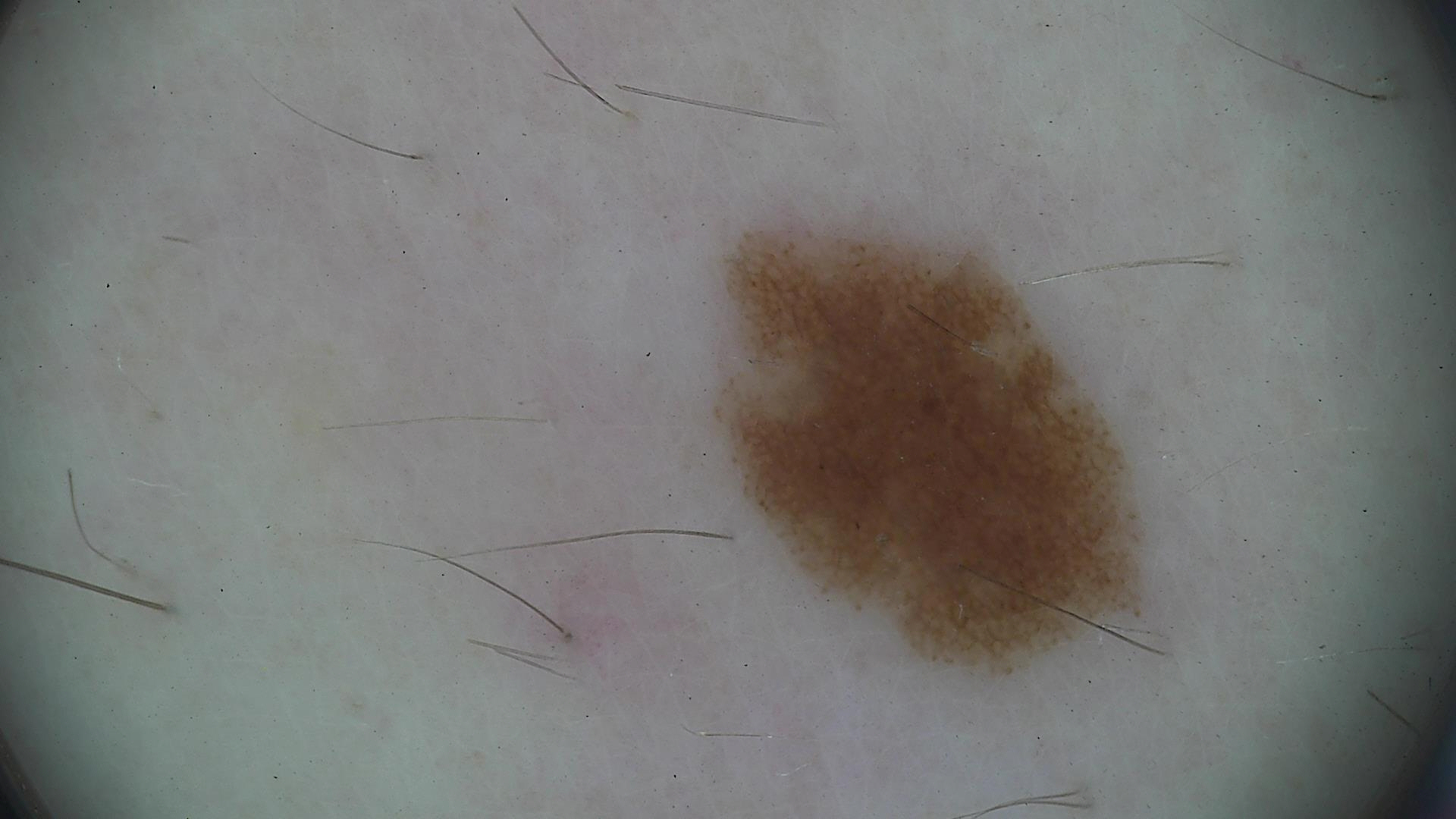imaging: dermoscopy; assessment: dysplastic junctional nevus (expert consensus).